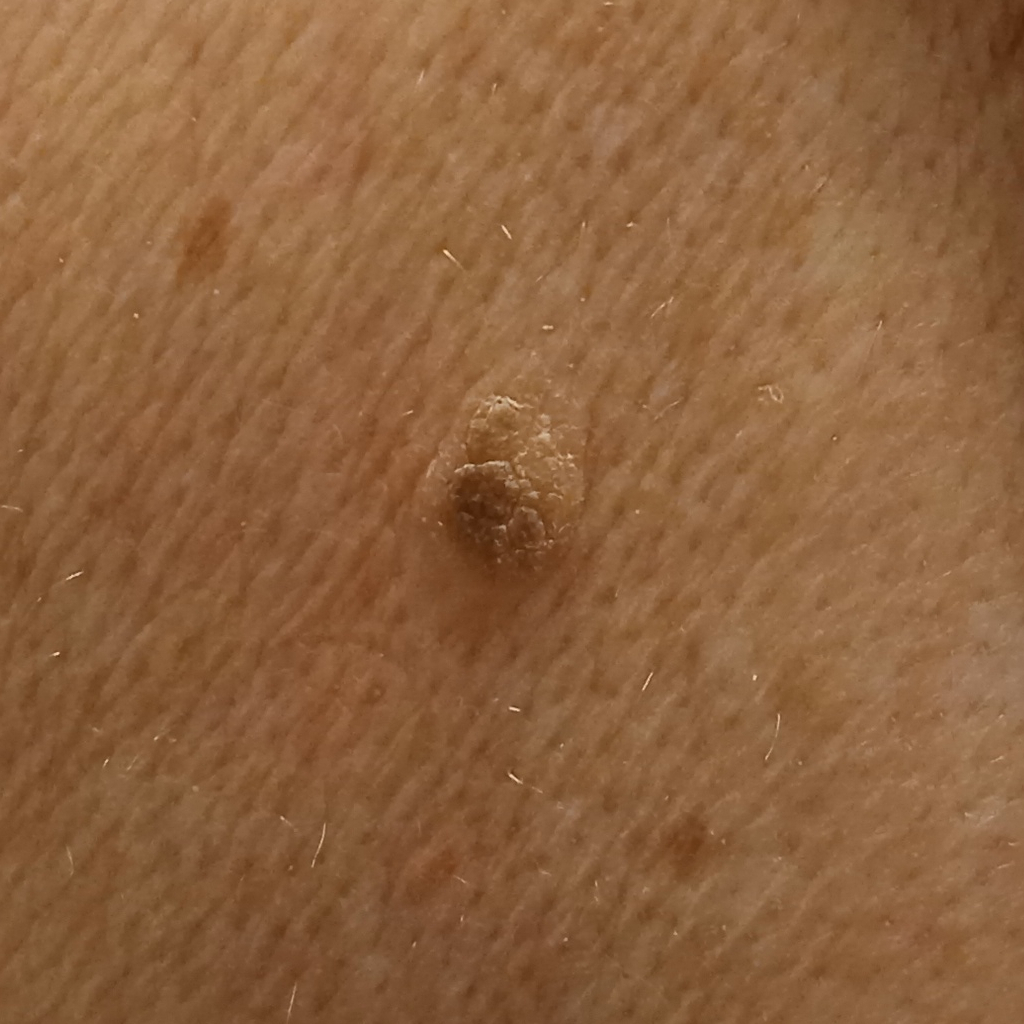subject — female, aged 73; referral context — research study (no referral diagnosis); imaging — clinical photo; site — the back; diagnostic label — seborrheic keratosis (dermatologist consensus).